The photograph was taken at an angle. The leg, arm, back of the torso, front of the torso and back of the hand are involved: 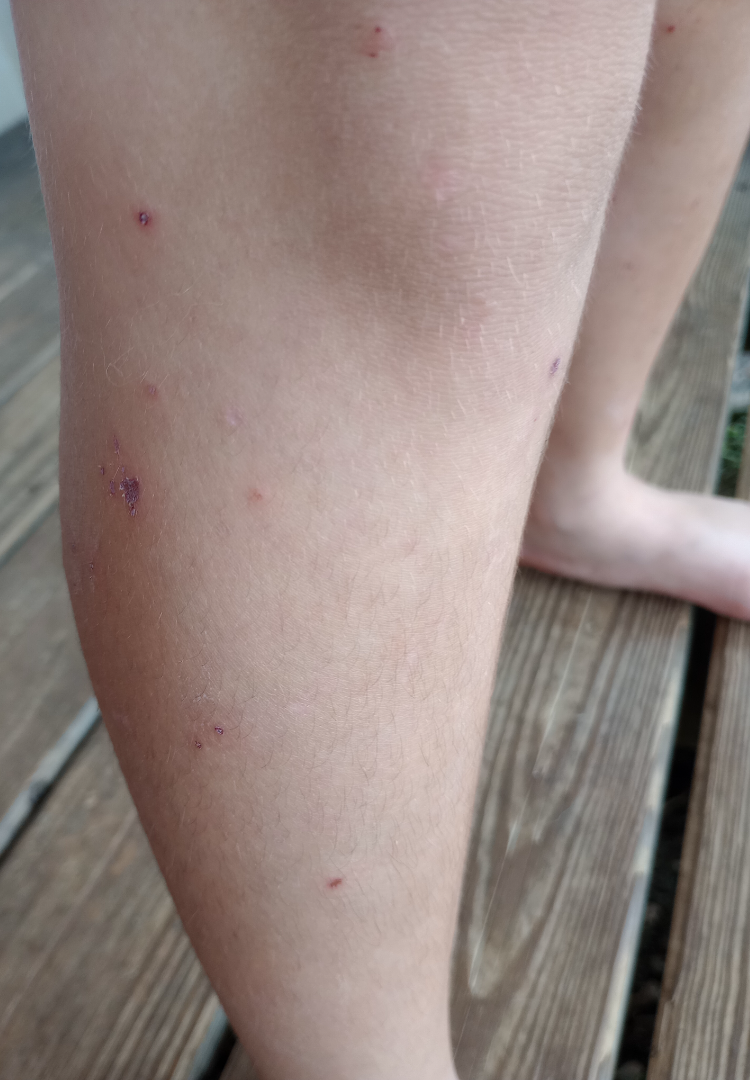Review: The dermatologist could not determine a likely condition from the photograph alone.